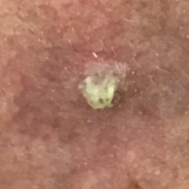Recorded as Fitzpatrick phototype II. The lesion is on the face. The patient reports that the lesion itches, has grown, and is elevated, but does not hurt. Histopathology confirmed an actinic keratosis.